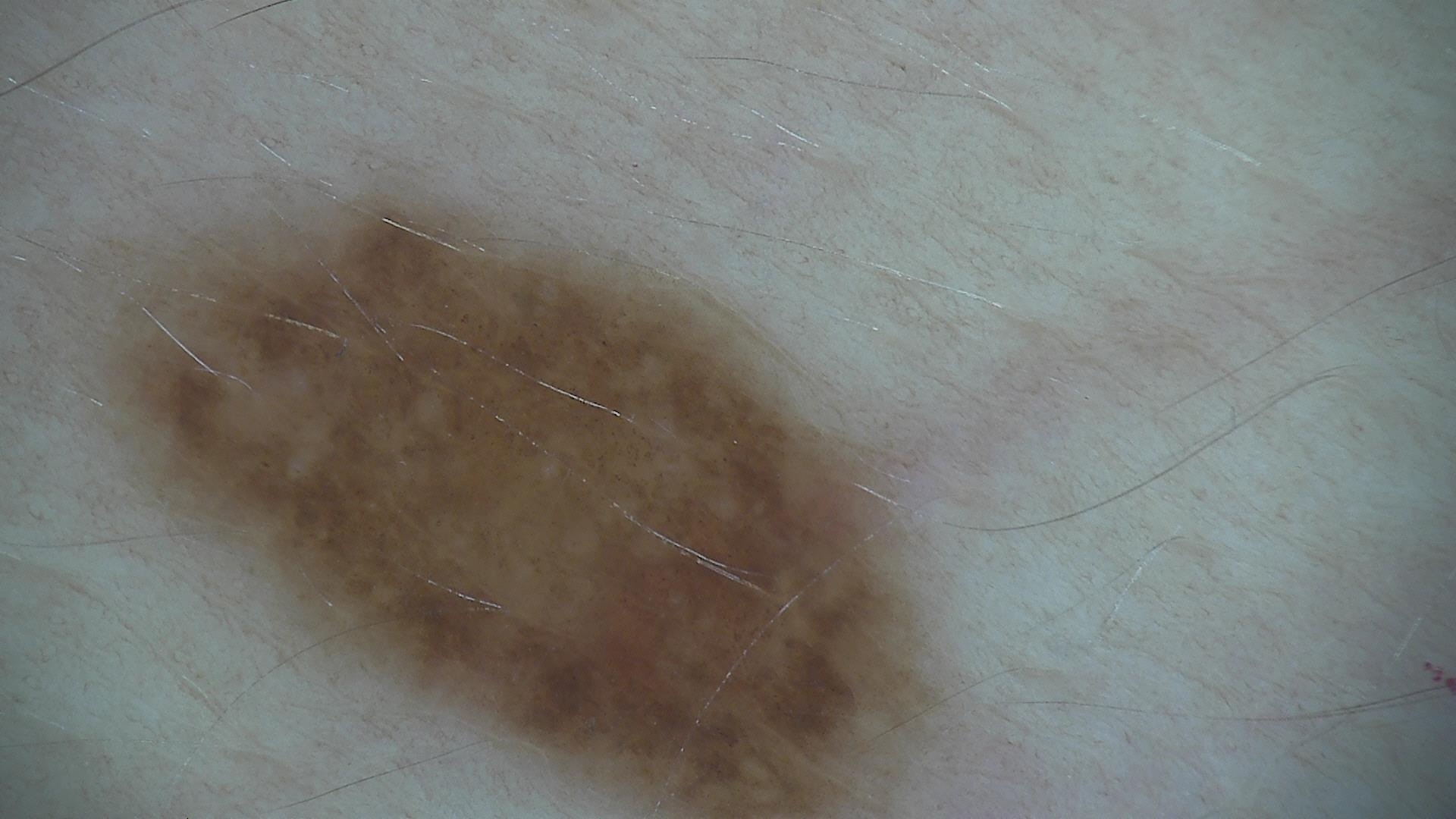<lesion>
  <diagnosis>
    <name>dysplastic junctional nevus</name>
    <code>jd</code>
    <malignancy>benign</malignancy>
    <super_class>melanocytic</super_class>
    <confirmation>expert consensus</confirmation>
  </diagnosis>
</lesion>